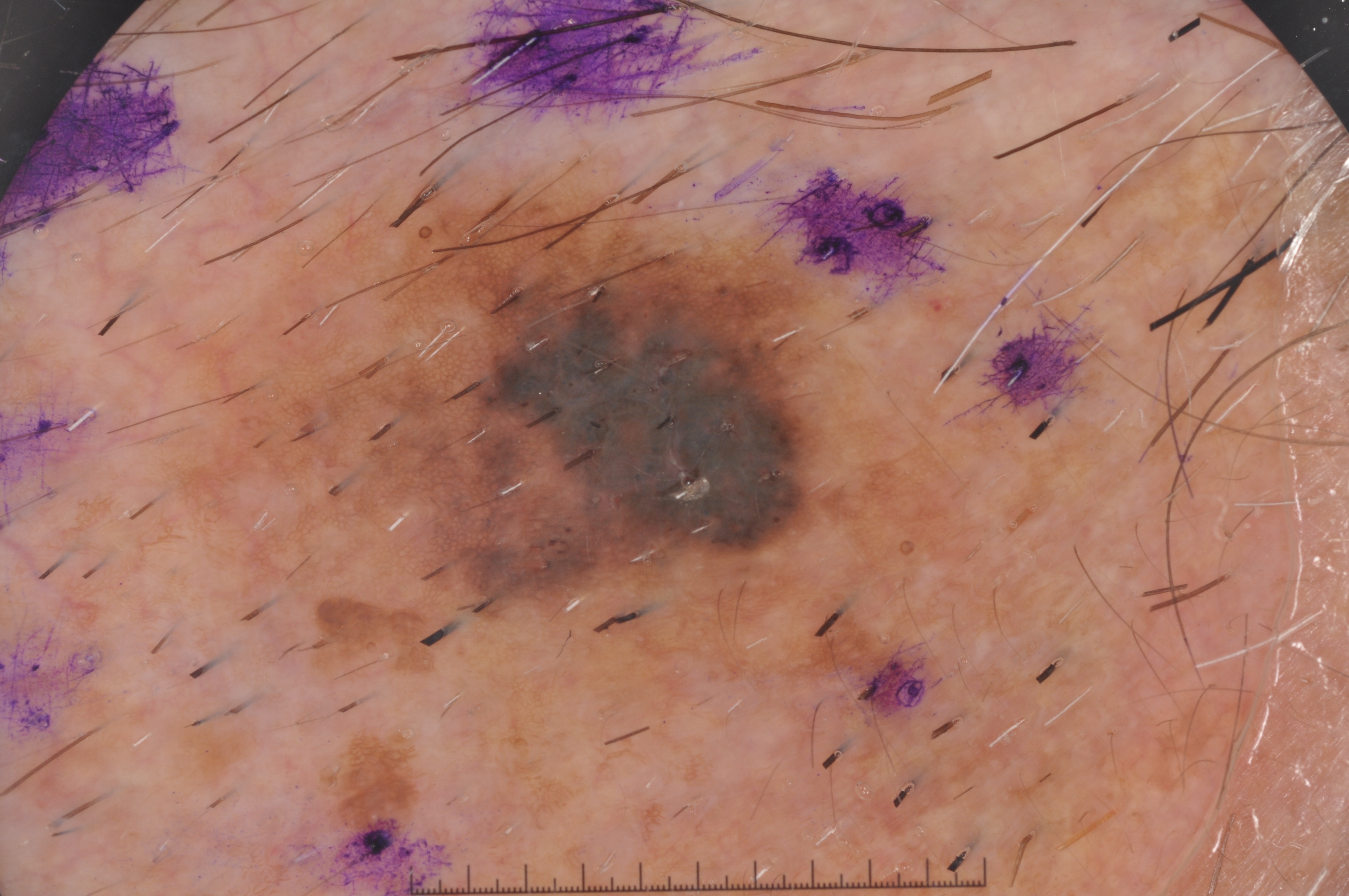Image and clinical context: A dermatoscopic image of a skin lesion. A male subject, roughly 80 years of age. The lesion spans x1=155 y1=141 x2=1055 y2=795. On dermoscopy, the lesion shows pigment network, with no negative network, streaks, or milia-like cysts. The lesion covers approximately 34% of the dermoscopic field. Conclusion: Histopathological examination showed a melanoma, a malignant lesion.